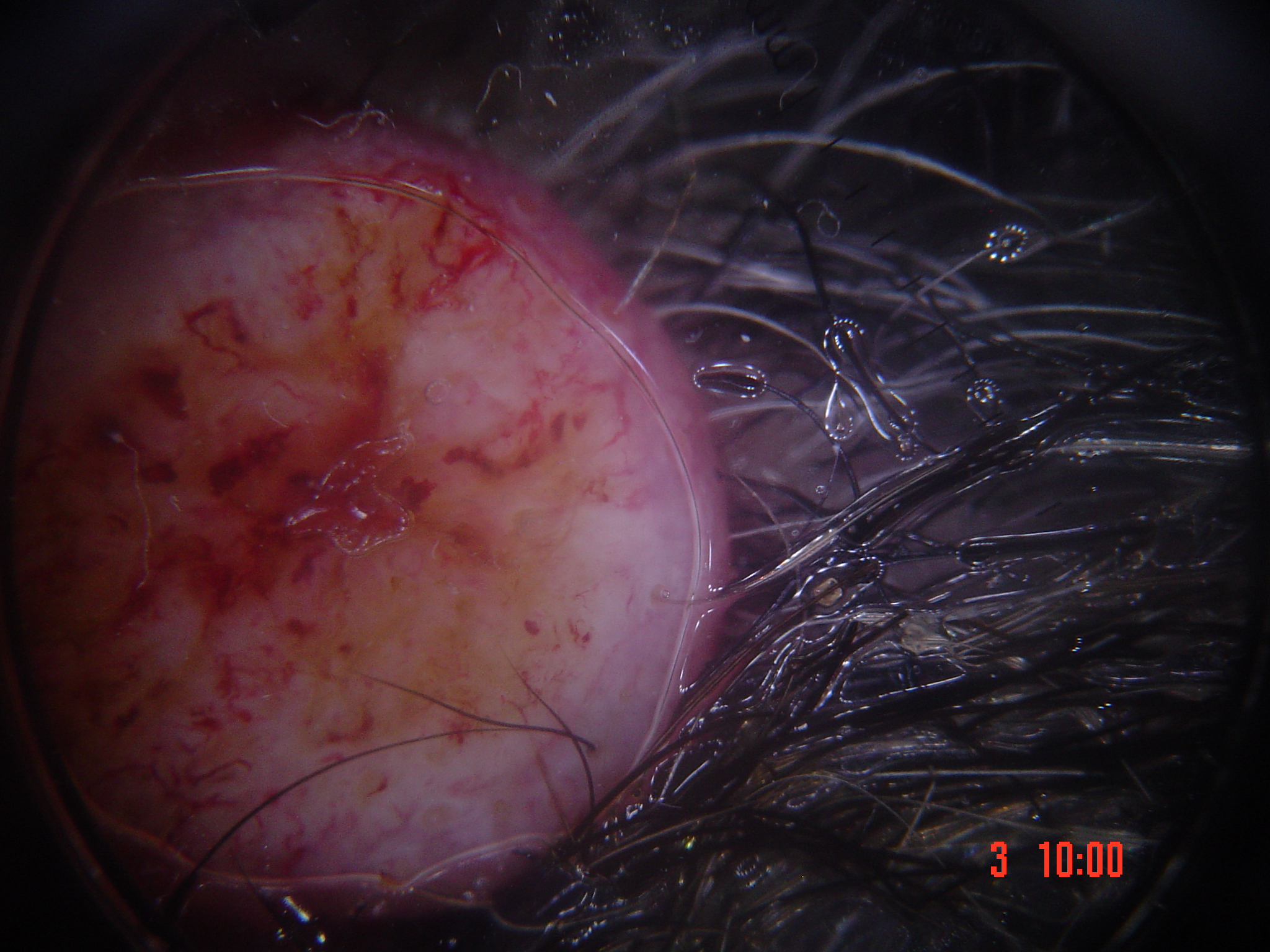Summary:
This is a keratinocytic lesion.
Conclusion:
The biopsy diagnosis was a malignant lesion — a squamous cell carcinoma.